A dermatoscopic image of a skin lesion.
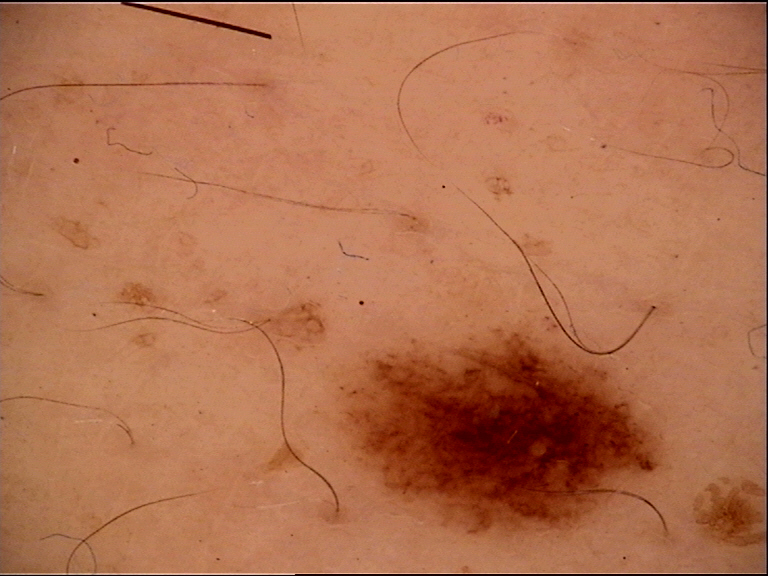Impression:
Classified as a dysplastic junctional nevus.